A clinical photograph showing a skin lesion · the patient was assessed as Fitzpatrick phototype II:
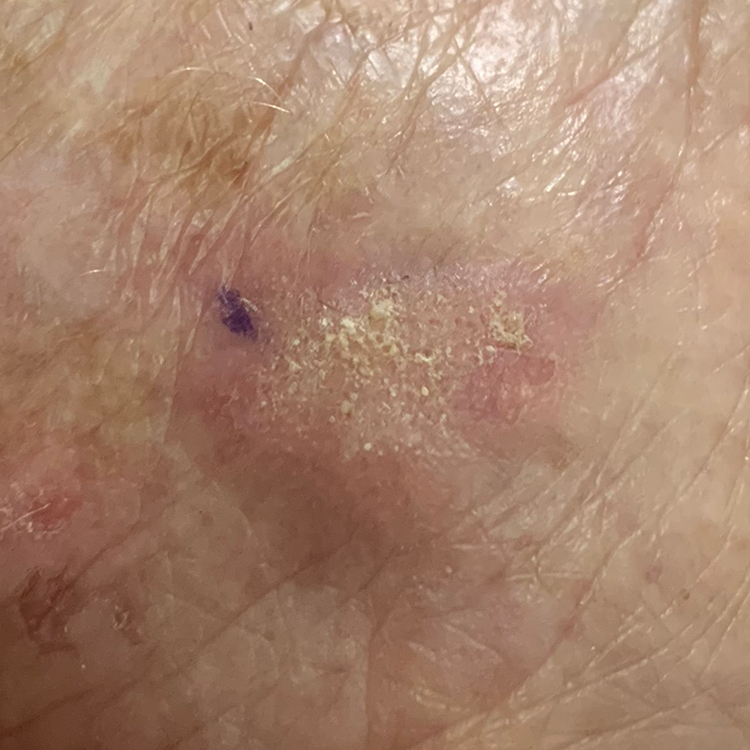anatomic site = a hand
size = 13 × 7 mm
symptoms = itching
diagnosis = actinic keratosis (biopsy-proven)